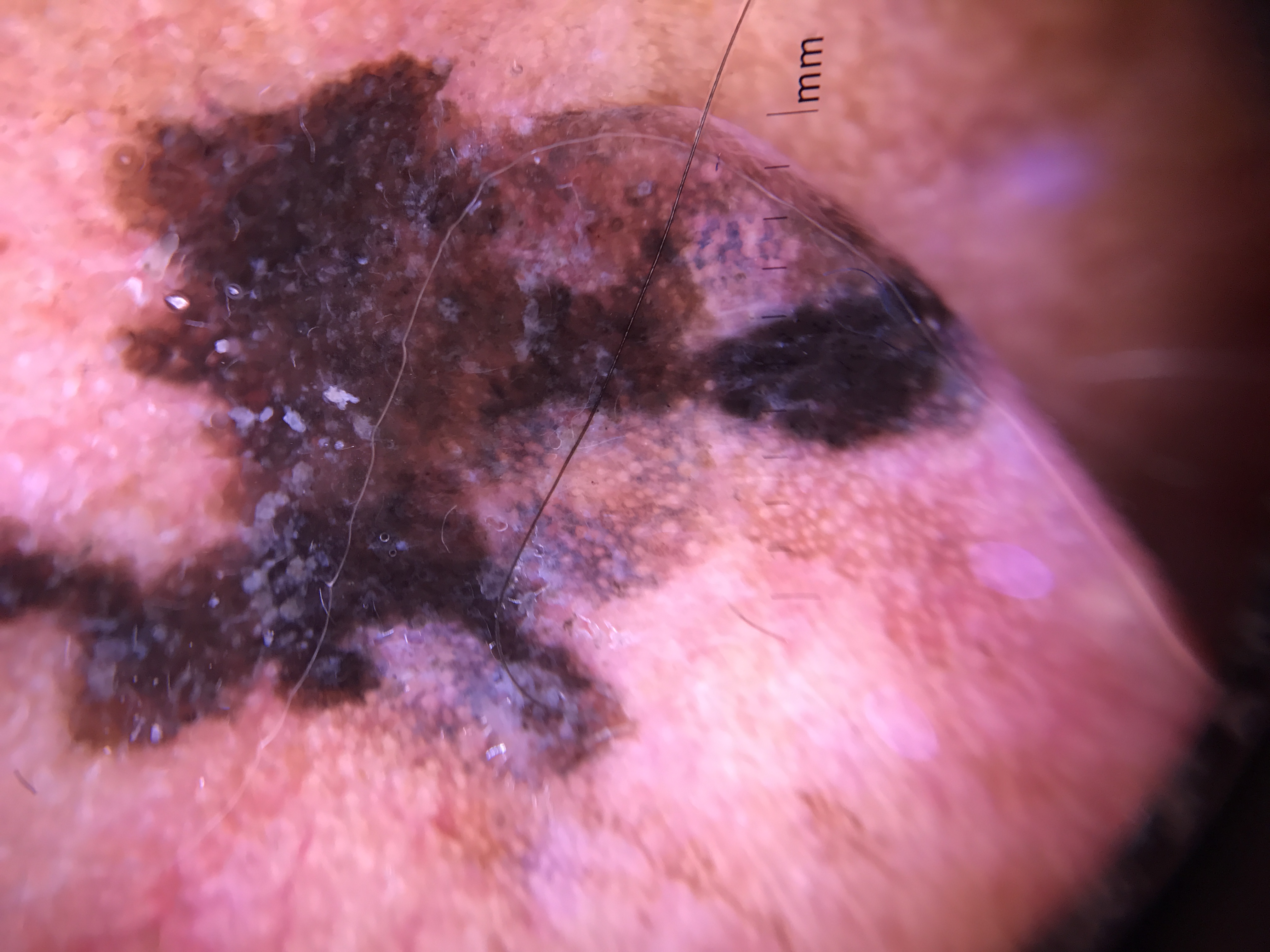A dermoscopic close-up of a skin lesion. The biopsy diagnosis was a skin cancer — a lentigo maligna.